A dermoscopic image of a skin lesion — 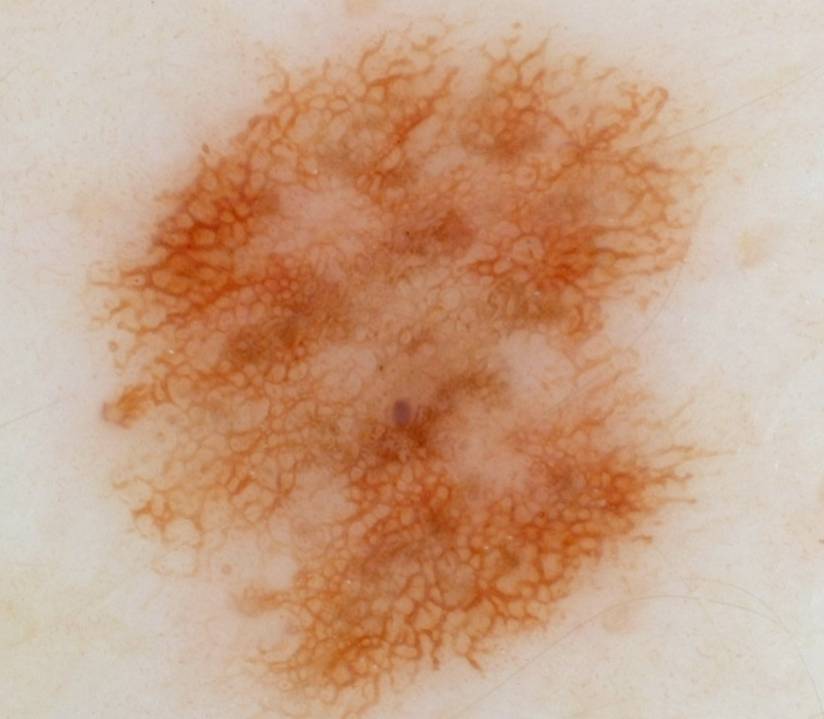The lesion is located at x1=92 y1=34 x2=694 y2=714. The dermoscopic pattern shows pigment network. A large lesion occupying much of the field. The clinical diagnosis was a melanocytic nevus, a benign skin lesion.